A dermoscopic image of a skin lesion; the patient is a female about 30 years old:
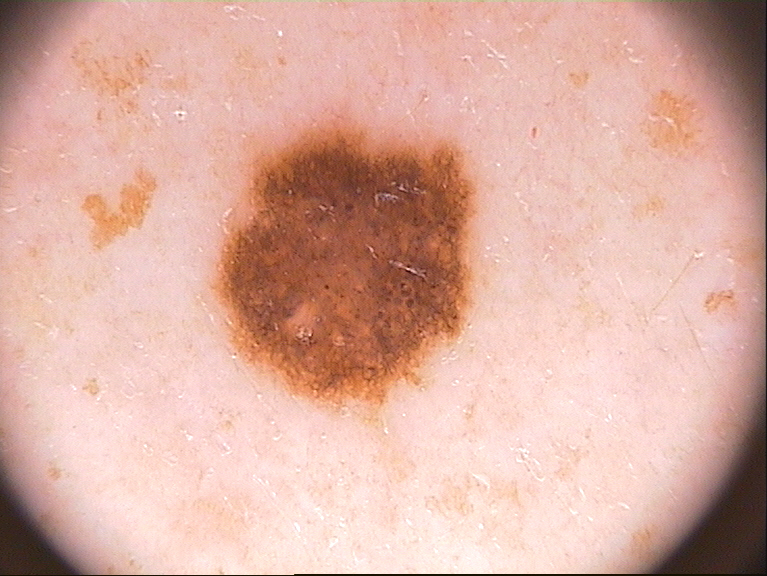features = globules and pigment network; absent: negative network, milia-like cysts, and streaks
lesion location = left=210, top=112, right=483, bottom=424
diagnostic label = a melanocytic nevus